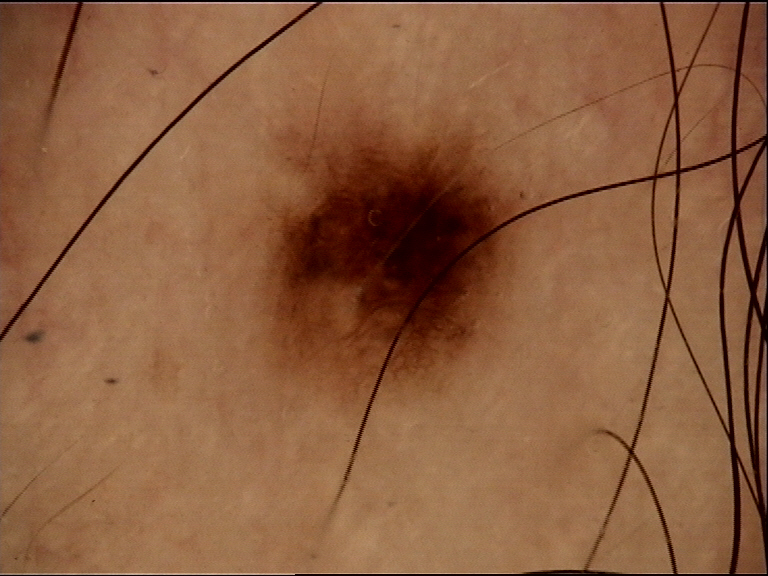Summary:
A skin lesion imaged with a dermatoscope.
Conclusion:
Labeled as a dysplastic junctional nevus.